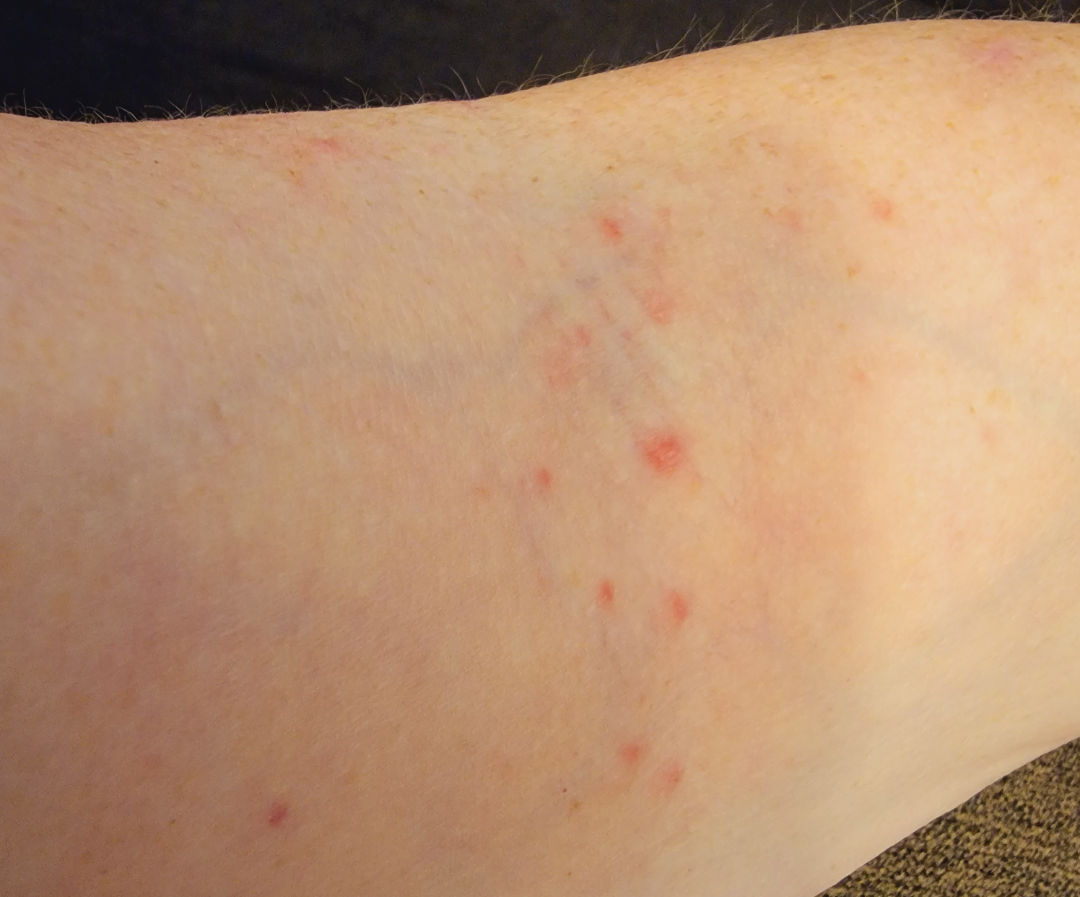The skin condition could not be confidently assessed from this image. The patient reported no relevant symptoms from the lesion. Present for one to four weeks. The arm is involved. The photograph is a close-up of the affected area. Self-categorized by the patient as a hair problem. No relevant systemic symptoms. The contributor notes the lesion is raised or bumpy. Female patient, age 60–69.